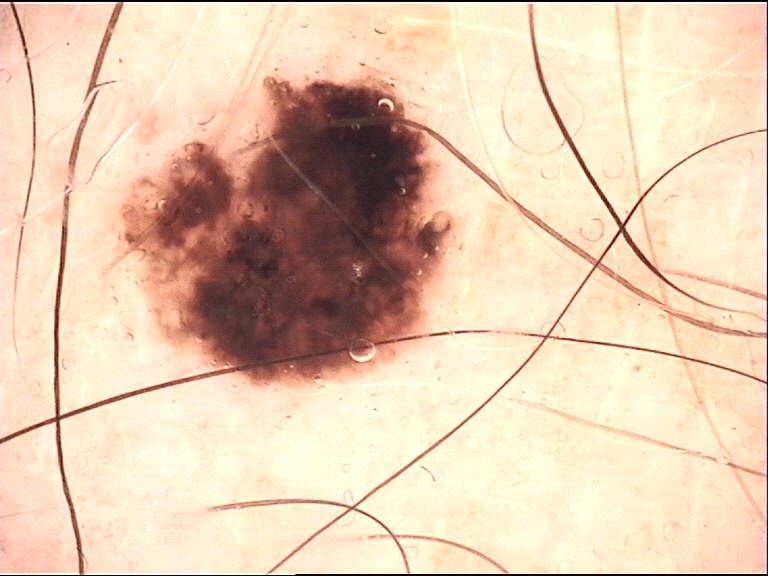Dermoscopy of a skin lesion. The diagnostic label was a dysplastic compound nevus.